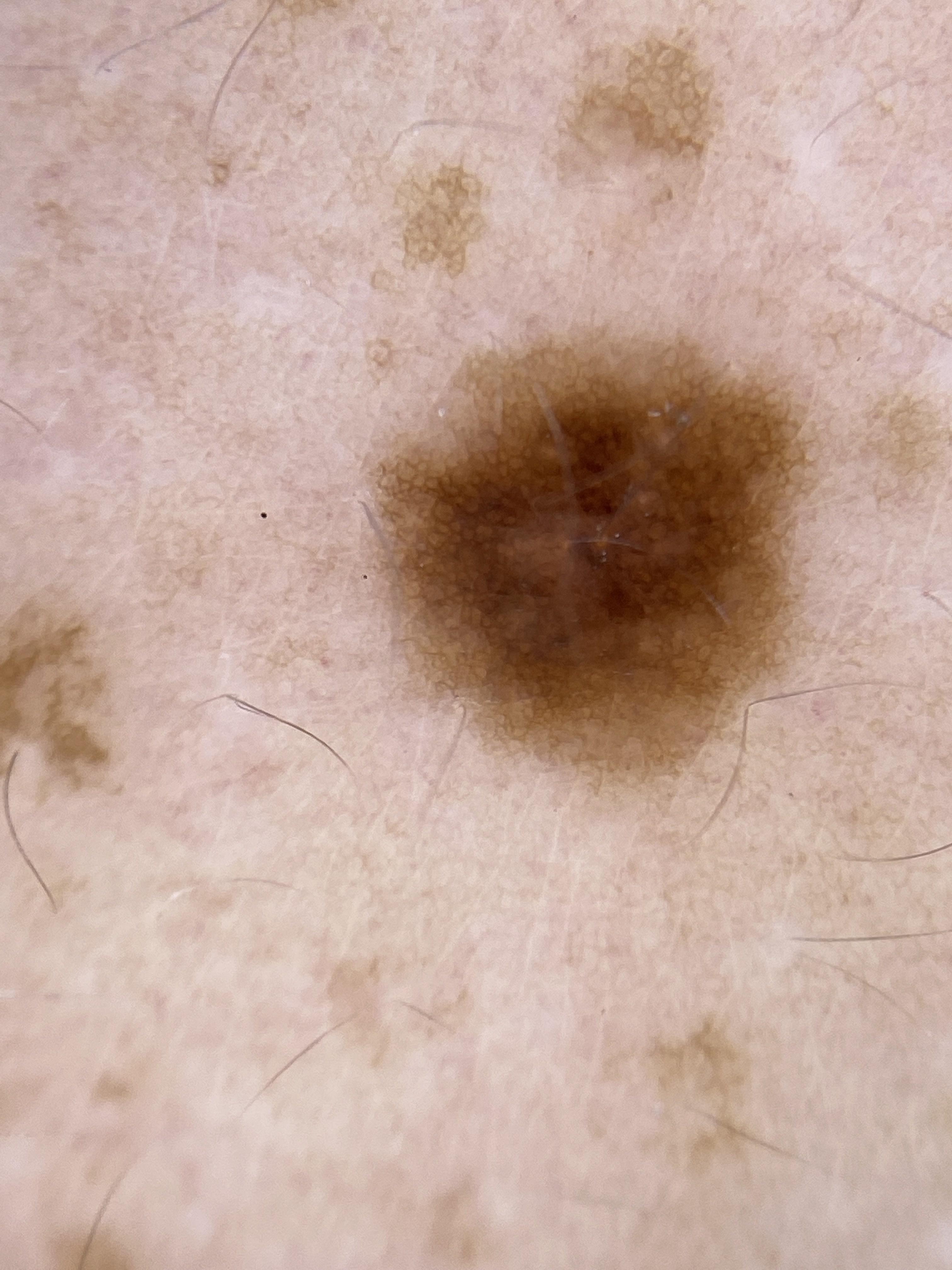Q: What are the patient's age and sex?
A: female, in their mid- to late 50s
Q: Skin phototype?
A: II
Q: Where on the body is the lesion?
A: the trunk
Q: What is the diagnosis?
A: Nevus (clinical impression)